A male patient about 40 years old · the patient was assessed as Fitzpatrick phototype II.
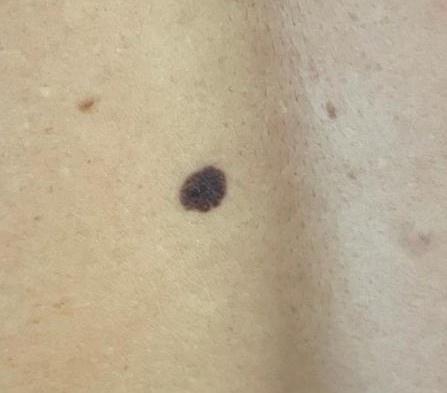Conclusion: The biopsy diagnosis was a nevus.